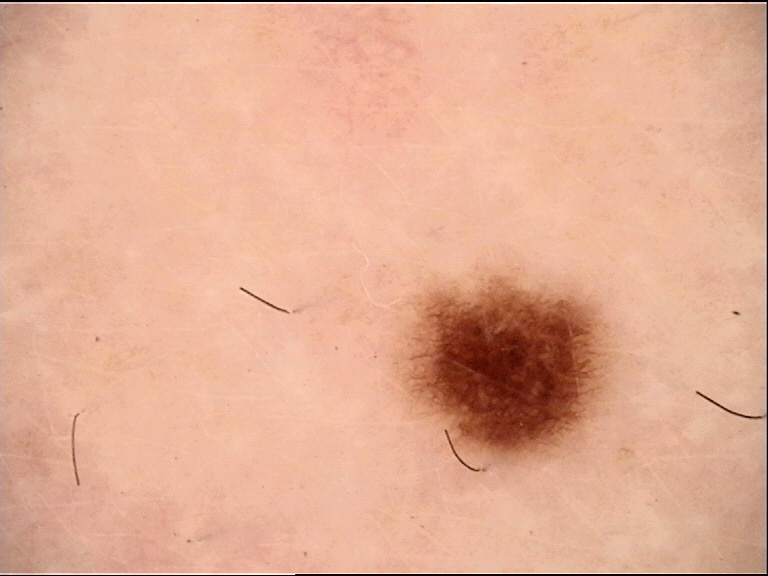Impression: The diagnosis was a junctional nevus.